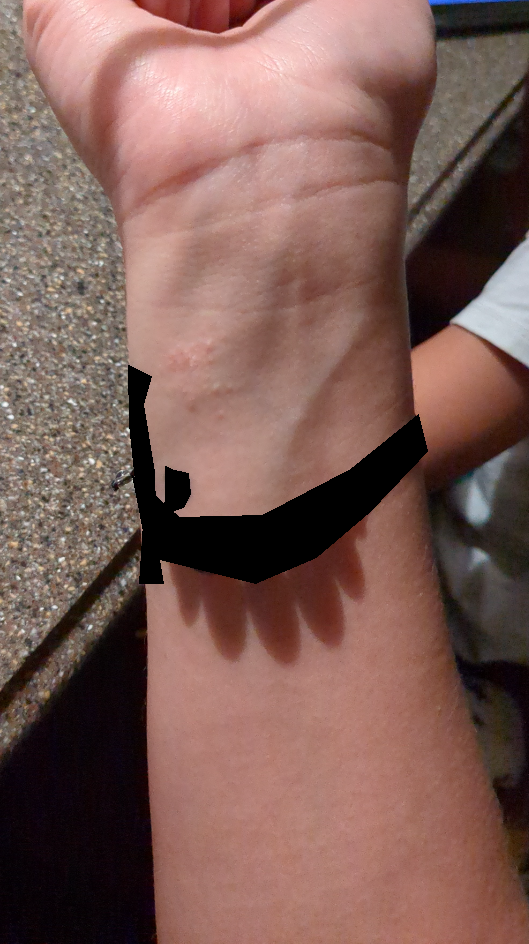Background: The lesion is described as fluid-filled, rough or flaky and raised or bumpy. The patient described the issue as a rash. An image taken at a distance. The patient notes associated fatigue. The patient notes itching and enlargement. The lesion involves the arm and leg. The subject is a female aged 18–29. Findings: Three dermatologists each reviewed the case: the leading consideration is Allergic Contact Dermatitis; the differential also includes Contact dermatitis; less likely is Eczema; less probable is Irritant Contact Dermatitis; lower on the differential is Herpes Simplex.